The photograph is a close-up of the affected area. Located on the leg.
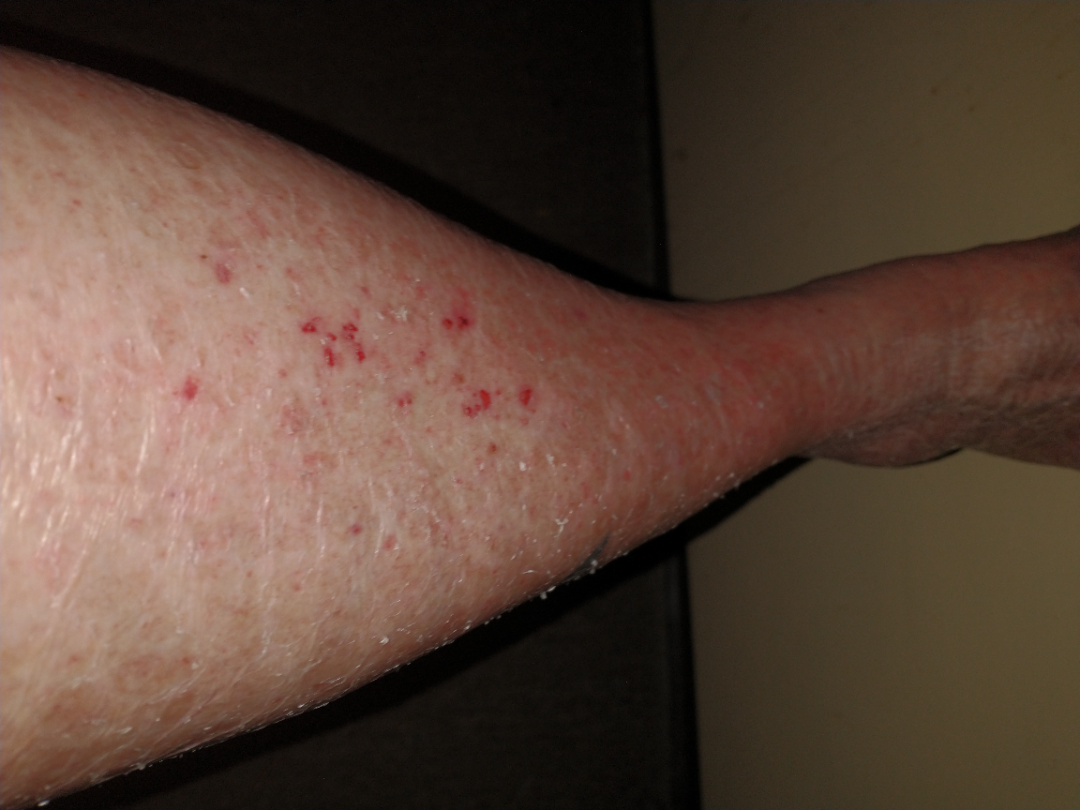differential diagnosis = Eczema (most likely); Stasis Dermatitis (possible); Ichthyosis (possible).